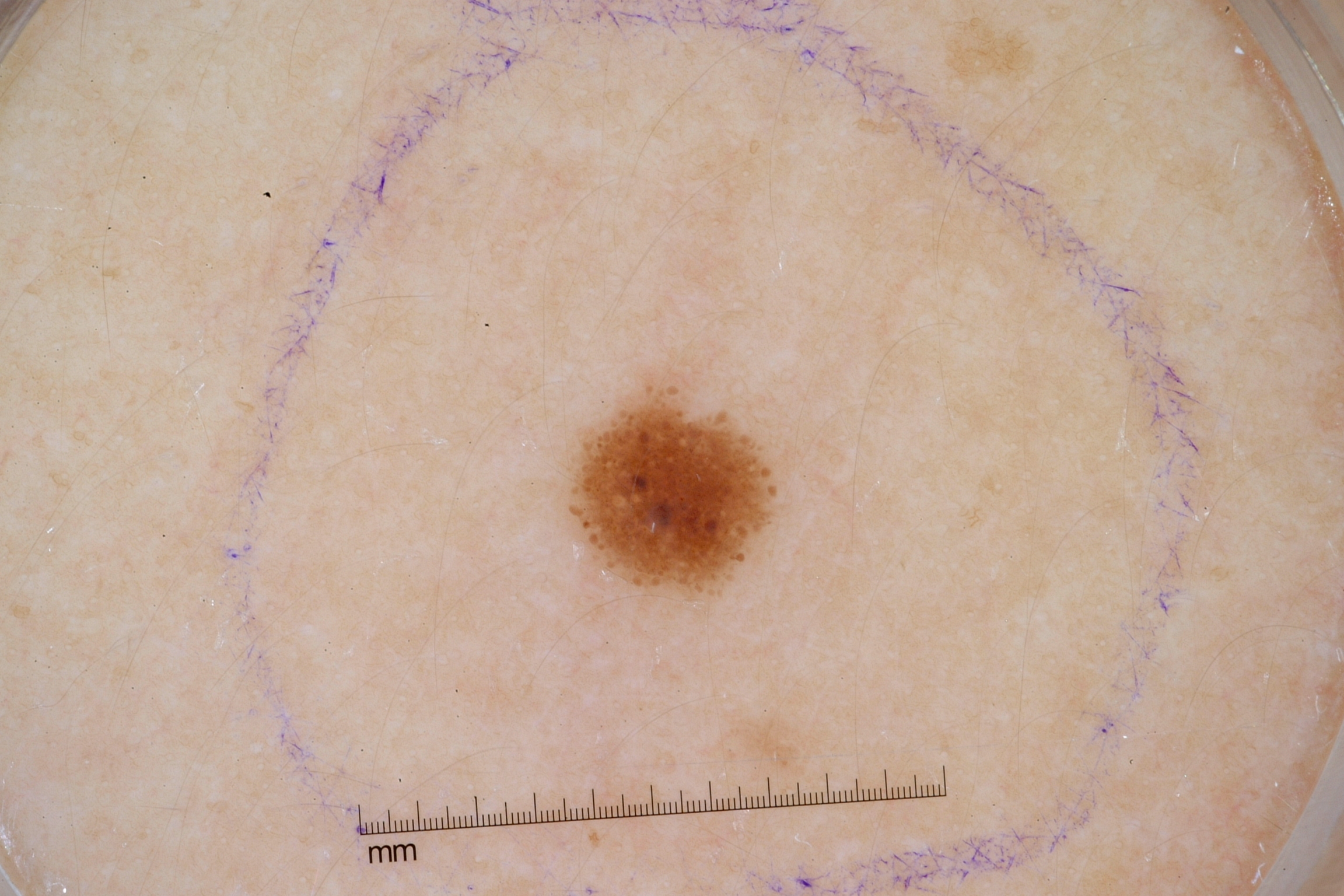Case summary:
A female subject aged 18 to 22. This is a dermoscopic photograph of a skin lesion. On dermoscopy, the lesion shows streaks. A small lesion within a wider field of skin. As (left, top, right, bottom), the visible lesion spans bbox(567, 392, 776, 595).
Impression:
The clinical diagnosis was a melanocytic nevus, a benign lesion.